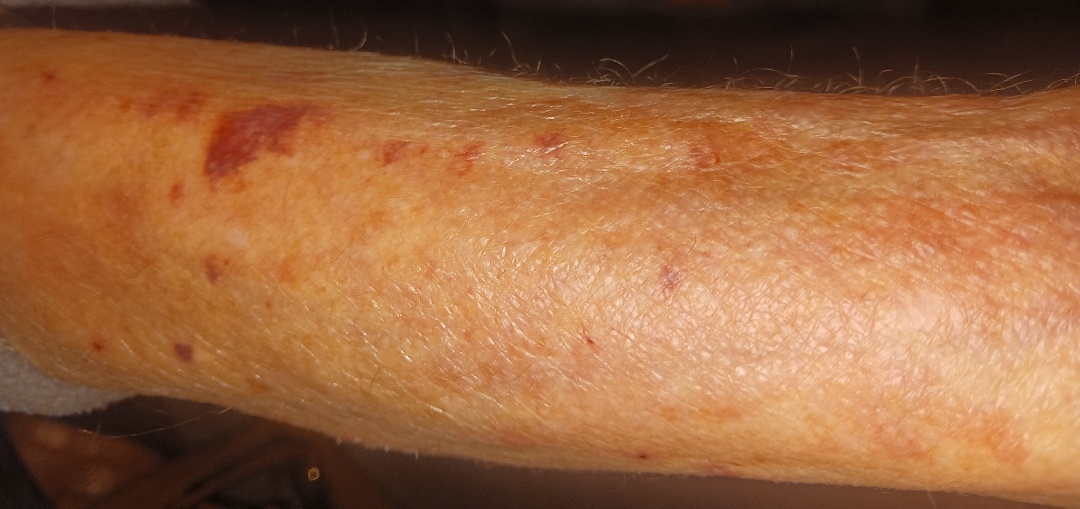location=leg, head or neck and arm; texture=raised or bumpy; framing=close-up.